The lesion involves the arm · the patient considered this a rash · symptoms reported: itching and darkening · skin tone: Fitzpatrick III; non-clinician graders estimated Monk skin tone scale 3 or 5 · the subject is 30–39, female · texture is reported as raised or bumpy and rough or flaky · an image taken at a distance · present for less than one week — 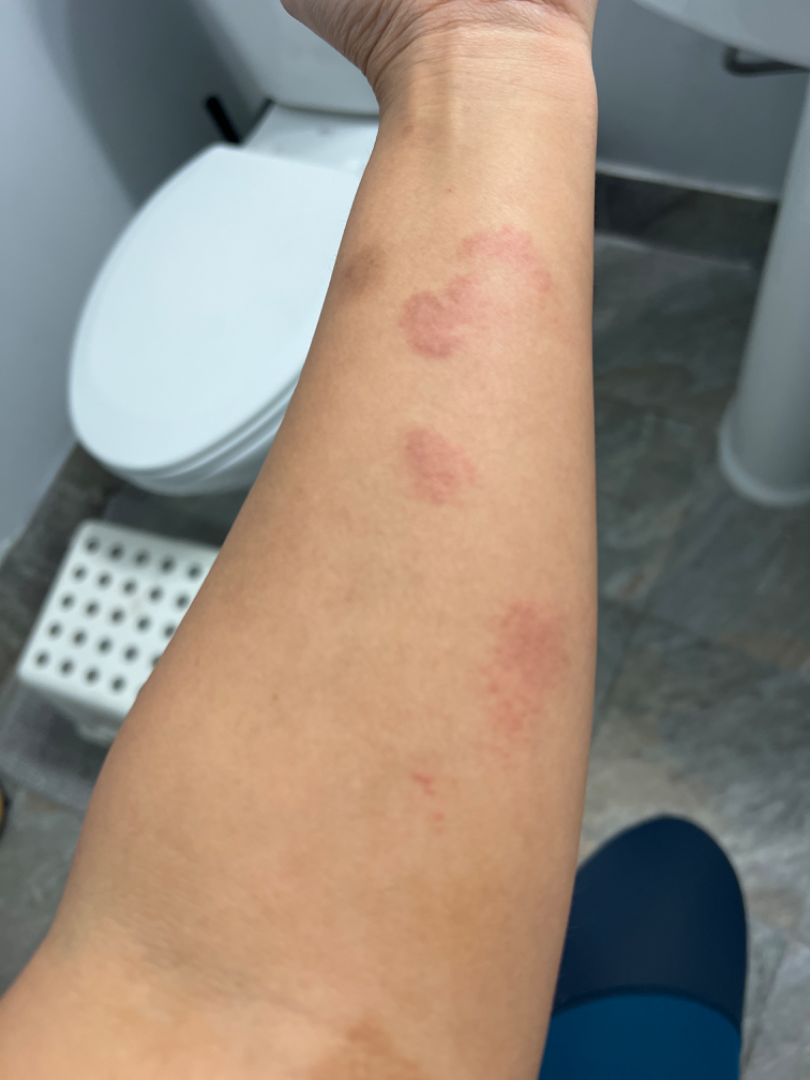clinical impression = three dermatologists each reviewed the case: the differential includes Eczema and Granuloma annulare, with no clear leading consideration; also raised was Tinea; an alternative is Erythema elevatum diutinum; less likely is Allergic Contact Dermatitis.